The lesion is described as rough or flaky · an image taken at a distance · the patient described the issue as a rash · the arm, leg and front of the torso are involved · the patient indicates the condition has been present for three to twelve months:
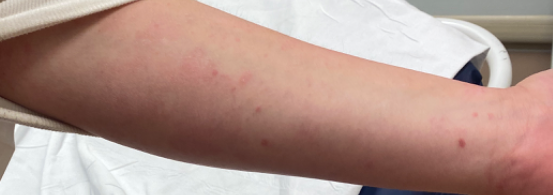The case was difficult to assess from the available photograph.